Present for three to twelve months, no associated systemic symptoms reported, a close-up photograph, the patient considered this a rash, the patient reports bothersome appearance, Fitzpatrick skin type V; non-clinician graders estimated Monk Skin Tone 6 (US pool) or 5 (India pool), the lesion is described as raised or bumpy and rough or flaky, the subject is male, the lesion involves the top or side of the foot.
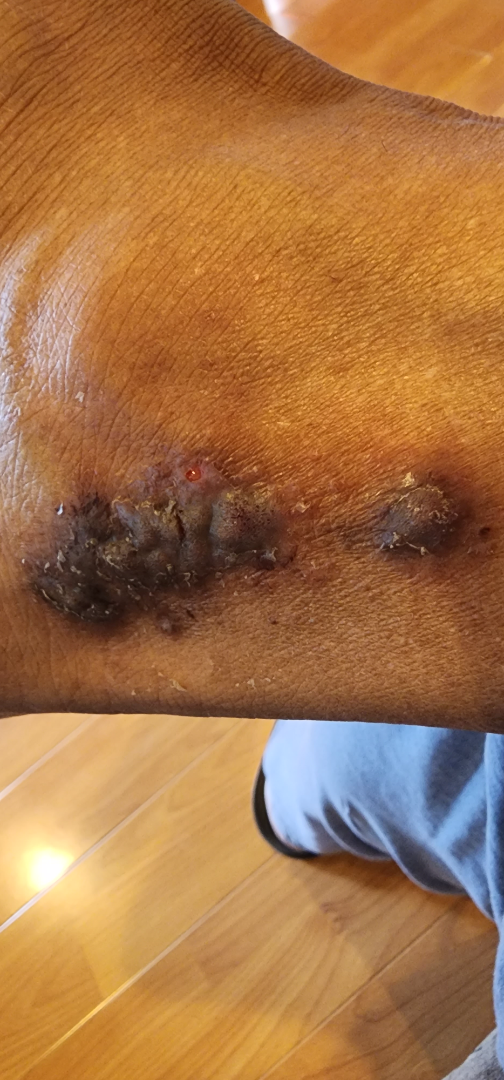The favored diagnosis is Kaposi's sarcoma of skin; lower on the differential is Psoriasis; a more distant consideration is Lichen Simplex Chronicus; less probable is Lichen planus/lichenoid eruption; less likely is Hemangioma; a remote consideration is Melanoma.